By history, prior skin cancer (patient or family), pesticide exposure, and no tobacco use · a female subject 57 years old · a clinical photo of a skin lesion taken with a smartphone · recorded as Fitzpatrick III:
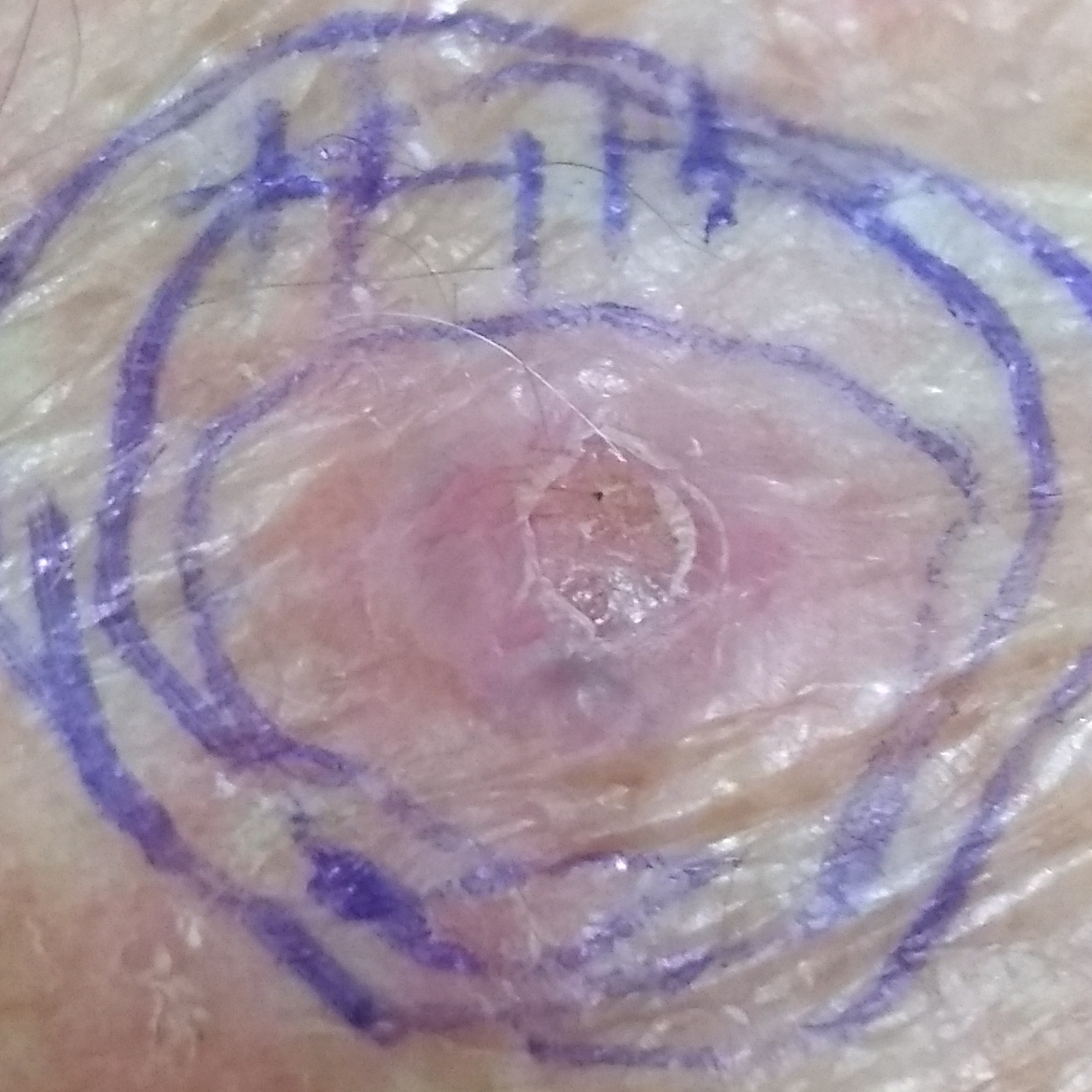Patient and lesion: The lesion was found on a hand. Measuring about 9 × 9 mm. Per patient report, the lesion is elevated, has bled, and has grown. Diagnosis: Biopsy-confirmed as a malignant lesion — a basal cell carcinoma.